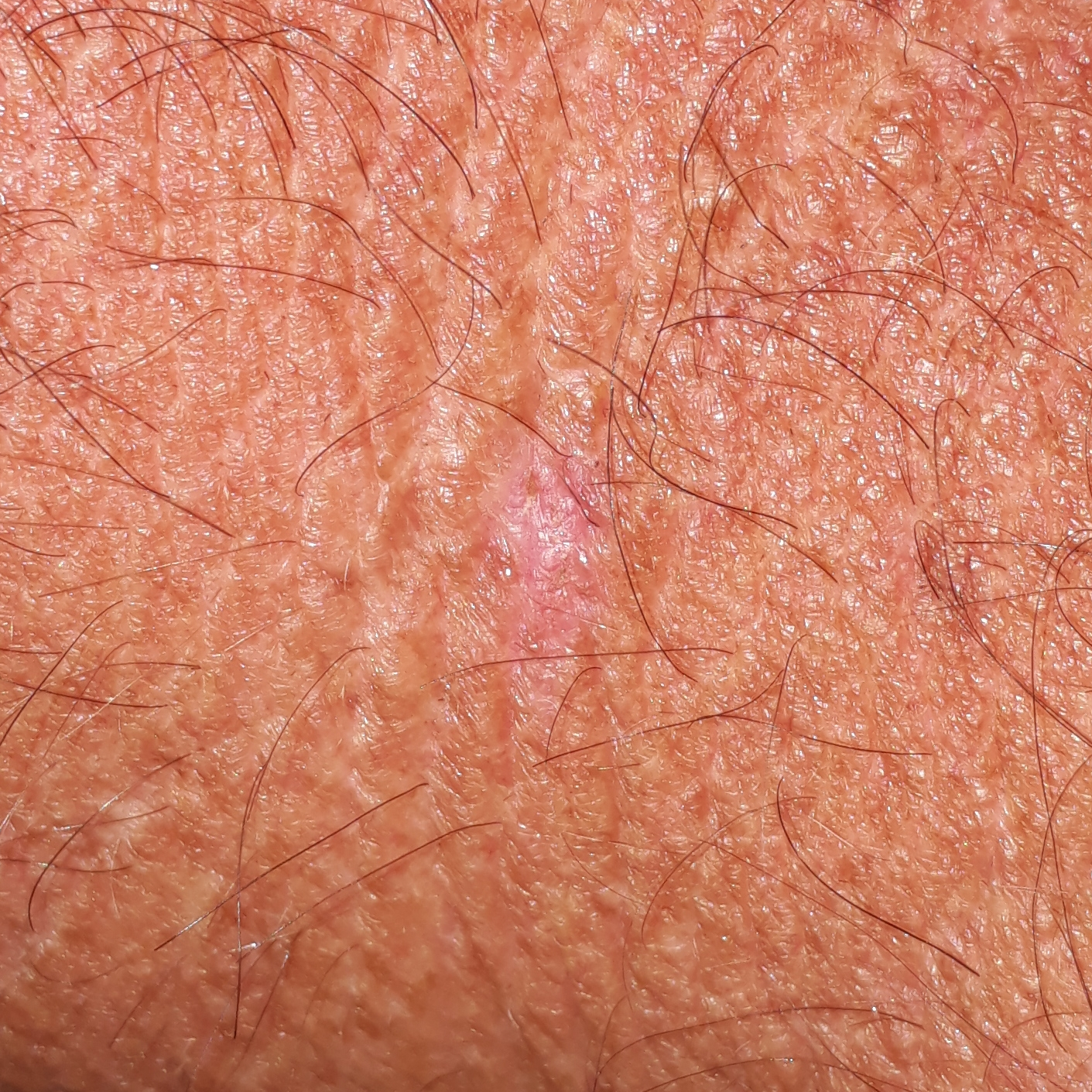subject = age 45; image type = clinical photo; region = the neck; reported symptoms = itching, elevation; impression = actinic keratosis (clinical consensus).